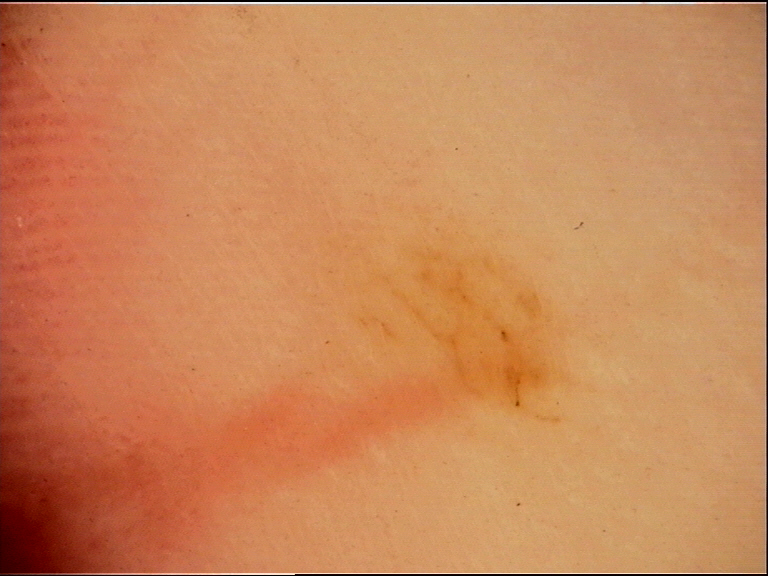A dermoscopic photograph of a skin lesion.
Labeled as an acral dysplastic junctional nevus.